An image taken at an angle:
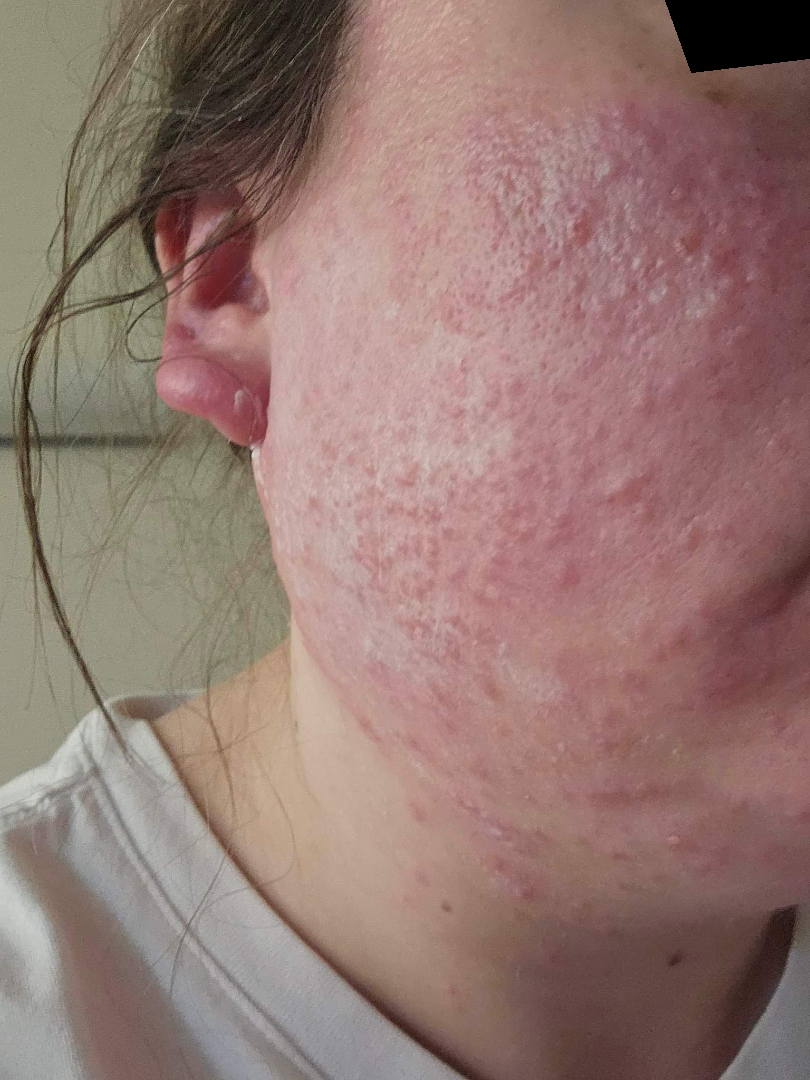Q: What is the dermatologist's impression?
A: a single dermatologist reviewed the case: the leading impression is Rosacea; also on the differential is Acne